The arm, front of the torso, leg and back of the torso are involved; a close-up photograph — 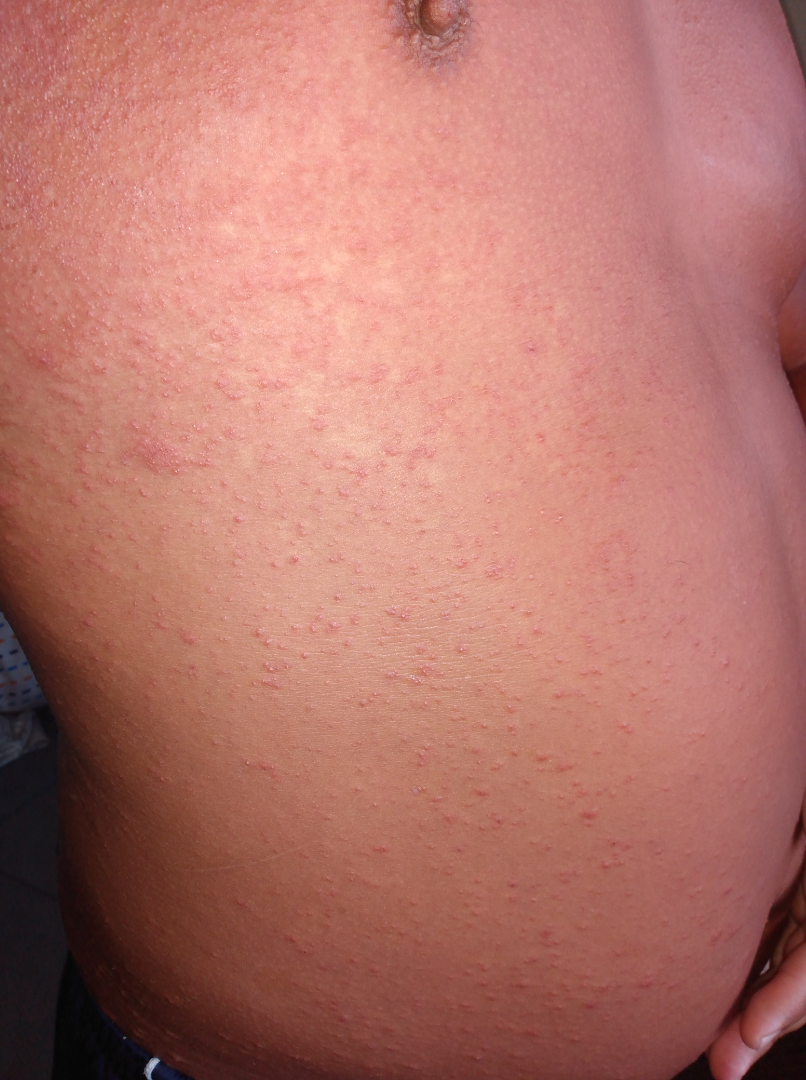The favored diagnosis is Viral Exanthem; also on the differential is Drug Rash; less likely is Hypersensitivity.